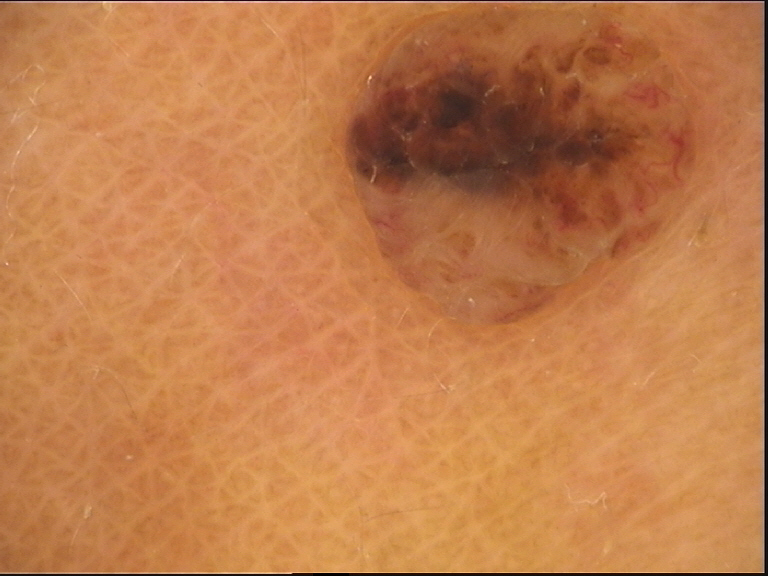Case: A dermoscopic close-up of a skin lesion. This is a banal lesion. Conclusion: The diagnostic label was a dermal nevus.